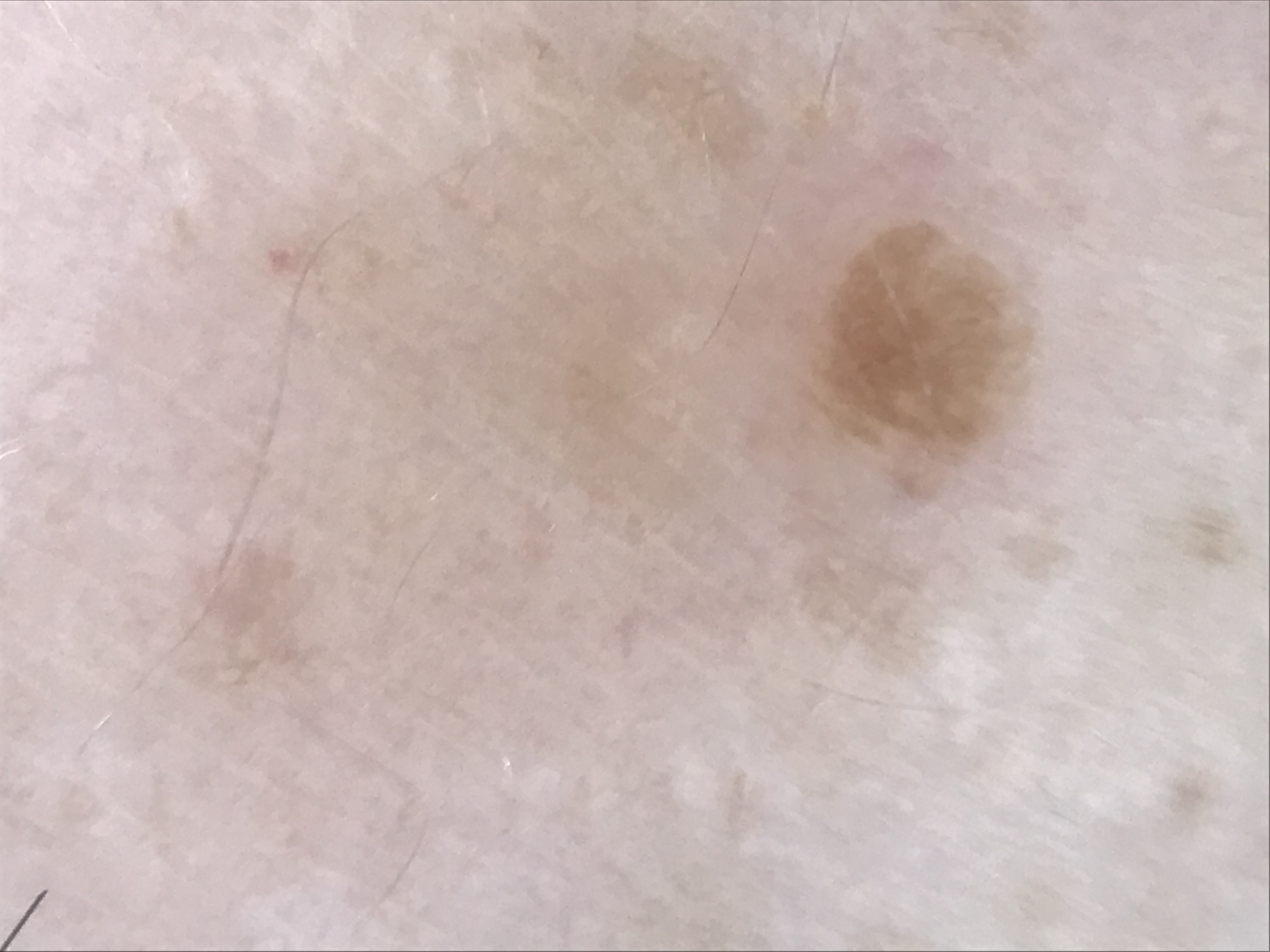A dermatoscopic image of a skin lesion. Diagnosed as a keratinocytic lesion — a seborrheic keratosis.